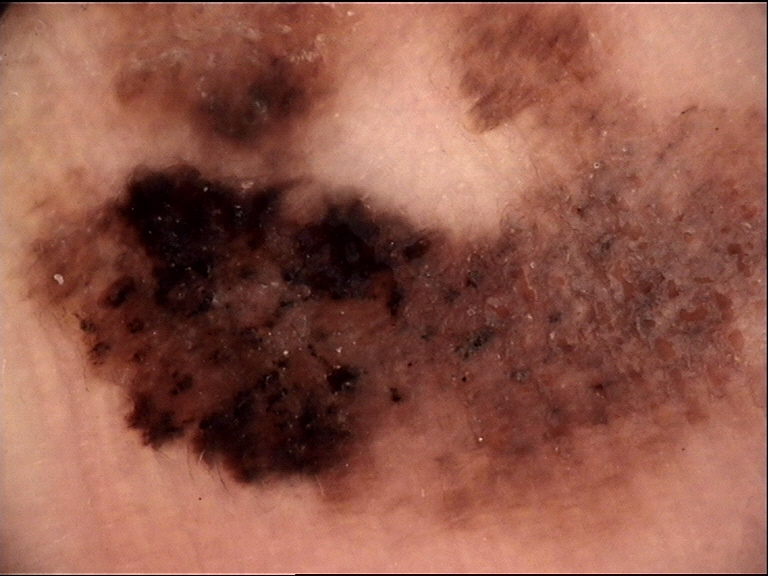Case: A dermoscopy image of a single skin lesion. Diagnosis: Histopathology confirmed an acral lentiginous melanoma.